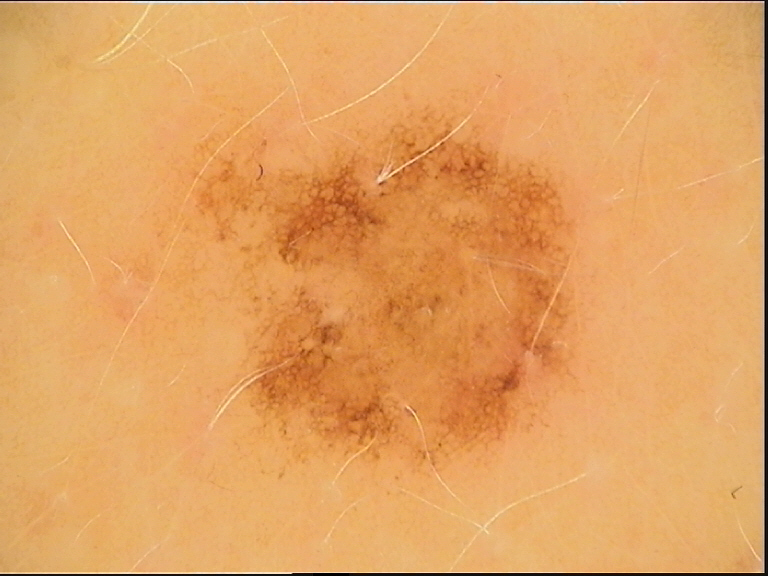Case:
– image: dermoscopy
– diagnosis: dysplastic junctional nevus (expert consensus)